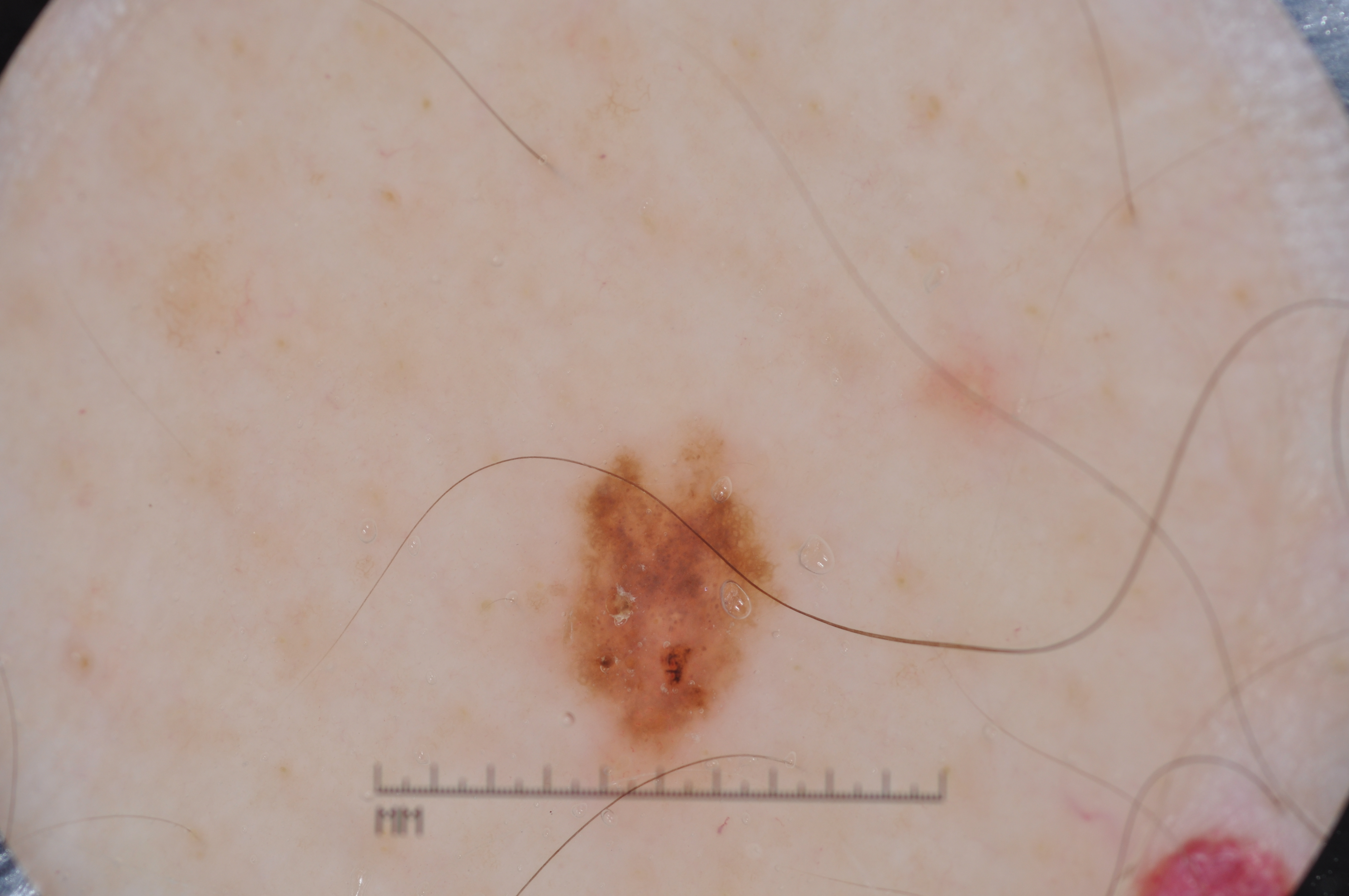Findings:
- image type: dermoscopic image
- patient: male, about 65 years old
- lesion extent: small
- dermoscopic features: pigment network, negative network, and milia-like cysts
- bounding box: x1=548, y1=441, x2=780, y2=749
- assessment: a melanocytic nevus